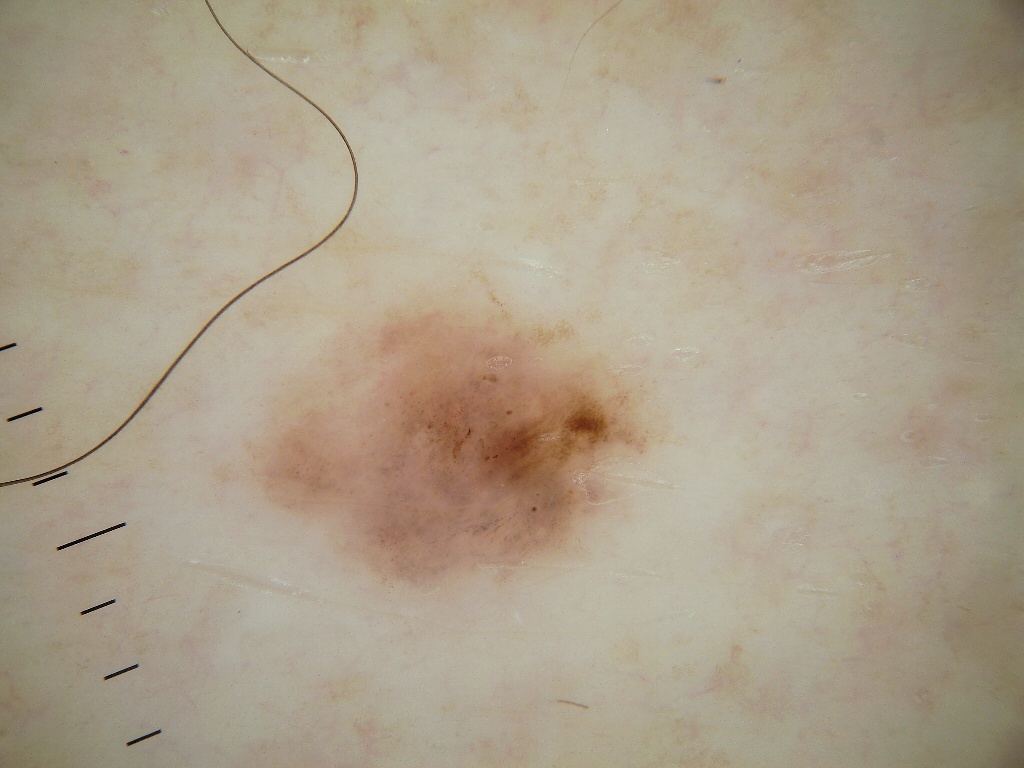image:
  modality: dermoscopy
patient:
  sex: male
  age_approx: 80
dermoscopic_features:
  present:
    - globules
  absent:
    - milia-like cysts
    - streaks
    - negative network
    - pigment network
lesion_location:
  bbox_xyxy:
    - 216
    - 307
    - 649
    - 594
lesion_extent: moderate
diagnosis:
  name: melanoma
  malignancy: malignant
  lineage: melanocytic
  provenance: histopathology